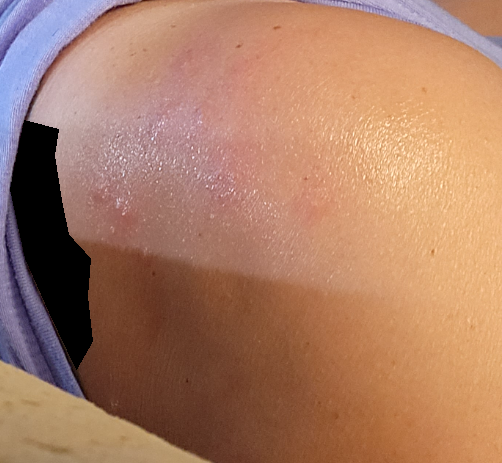Case summary:
• assessment · unable to determine